The contributor is a female aged 30–39, the head or neck is involved, the photograph was taken at an angle.
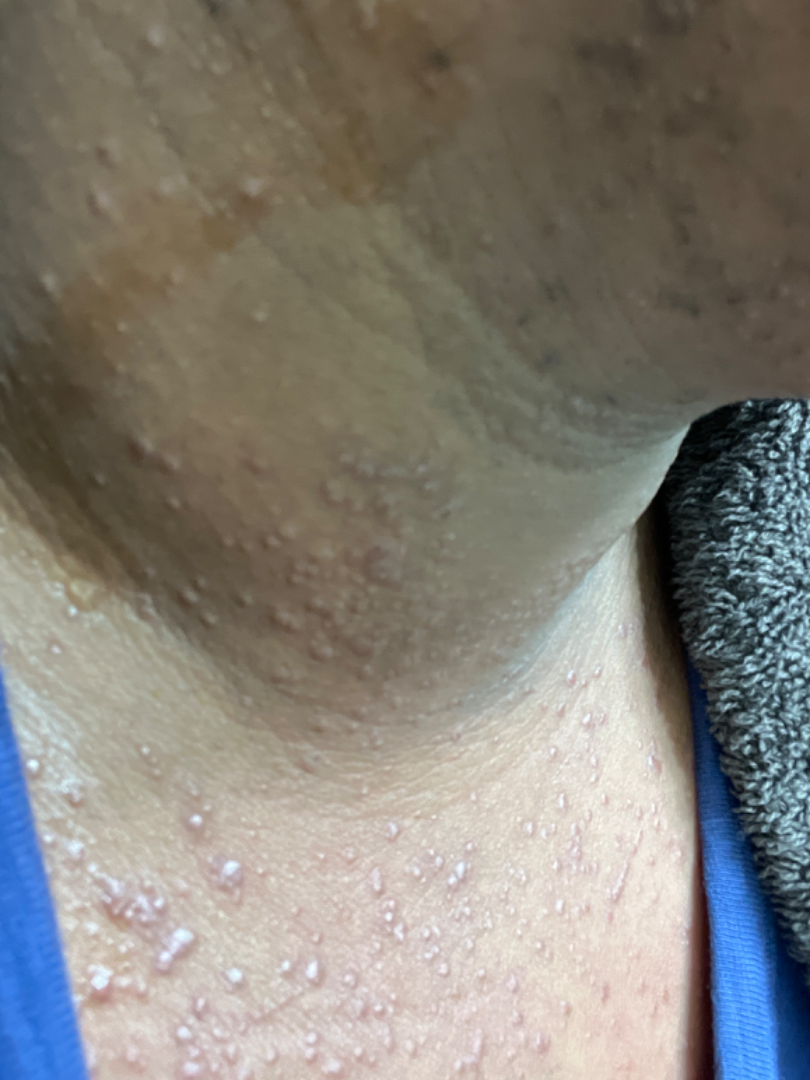<summary>
  <differential>
    <leading>Adnexal neoplasm</leading>
    <considered>Folliculitis, Miliaria</considered>
    <unlikely>Cyst, Lichen planus/lichenoid eruption</unlikely>
  </differential>
</summary>